A dermoscopy image of a single skin lesion: 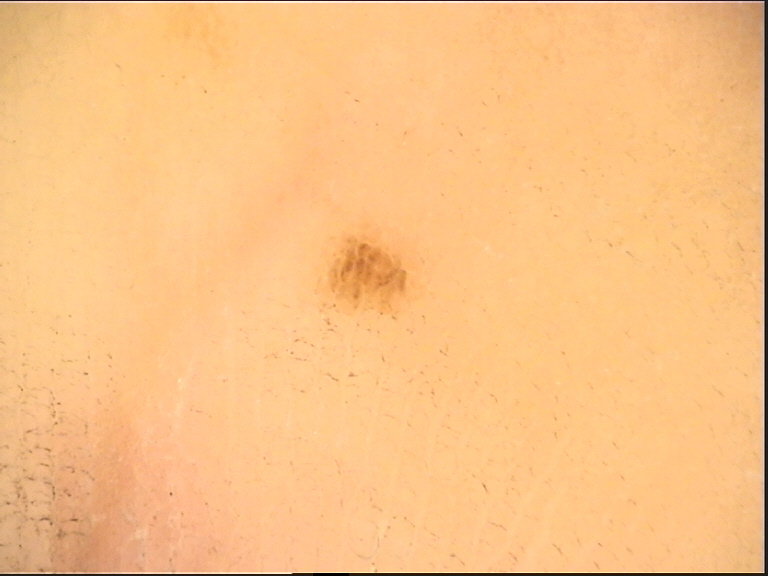category: banal | diagnostic label: acral junctional nevus (expert consensus).